A dermoscopic view of a skin lesion · a female patient, aged approximately 40:
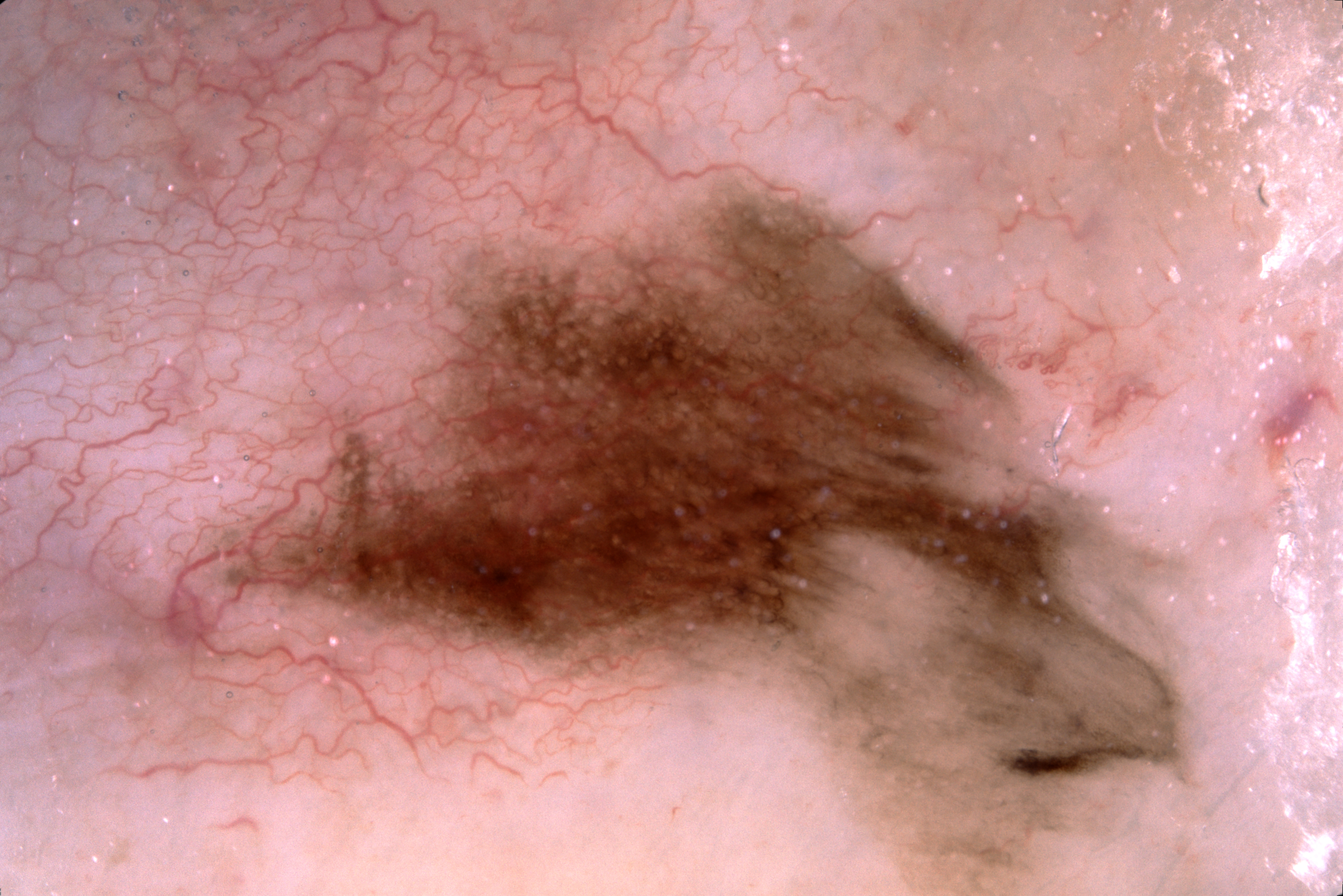dermoscopic_features:
  present: []
  absent:
    - negative network
    - milia-like cysts
    - streaks
    - pigment network
lesion_location:
  bbox_xyxy:
    - 162
    - 164
    - 1217
    - 894
diagnosis:
  name: melanocytic nevus
  malignancy: benign
  lineage: melanocytic
  provenance: clinical